The patient is a female approximately 70 years of age; this is a dermoscopic photograph of a skin lesion.
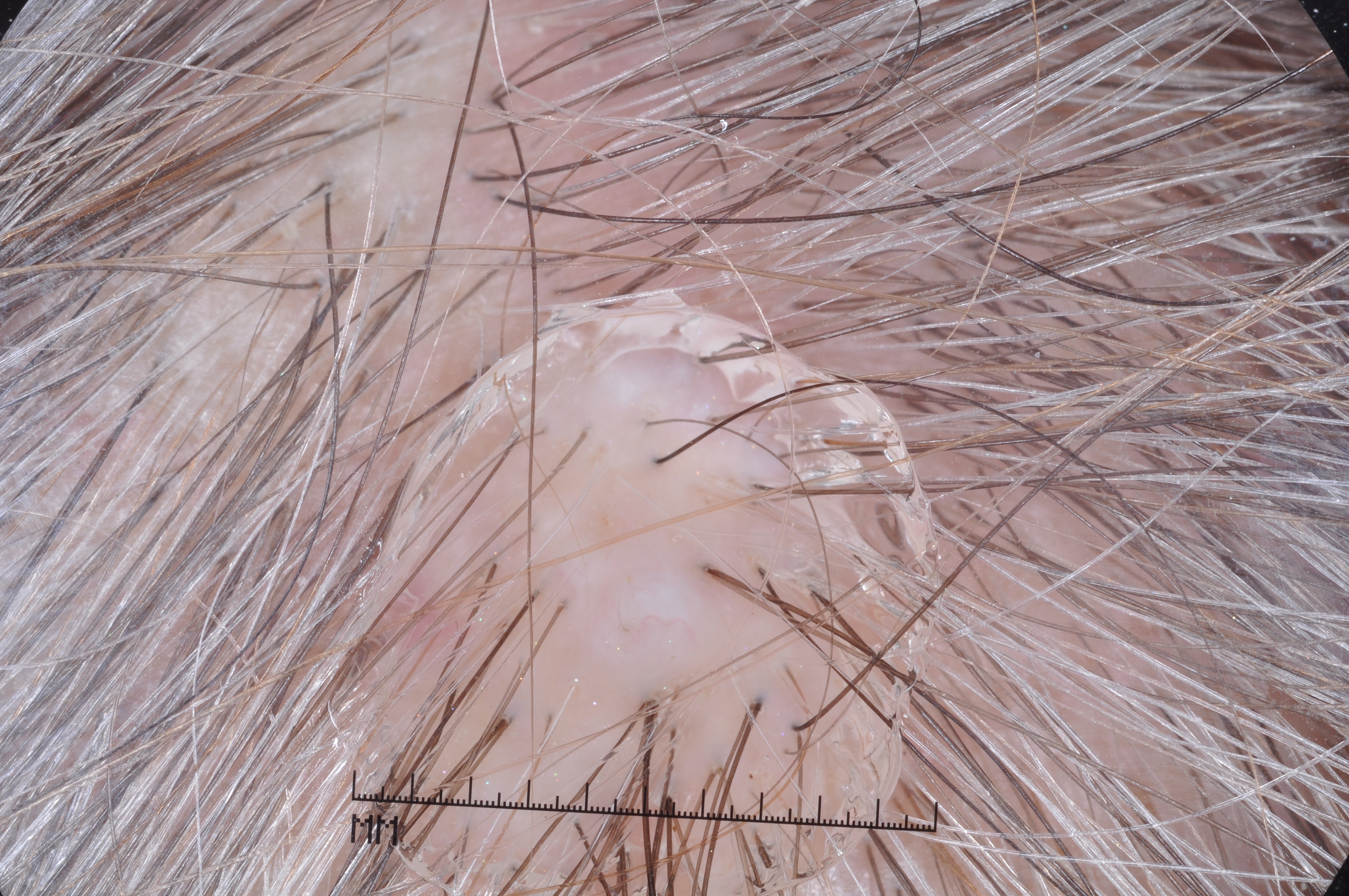{
  "lesion_extent": "moderate",
  "lesion_location": {
    "bbox_xyxy": [
      345,
      291,
      924,
      889
    ]
  },
  "dermoscopic_features": {
    "present": [],
    "absent": [
      "milia-like cysts",
      "pigment network",
      "negative network",
      "streaks"
    ]
  },
  "diagnosis": {
    "name": "melanocytic nevus",
    "malignancy": "benign",
    "lineage": "melanocytic",
    "provenance": "clinical"
  }
}